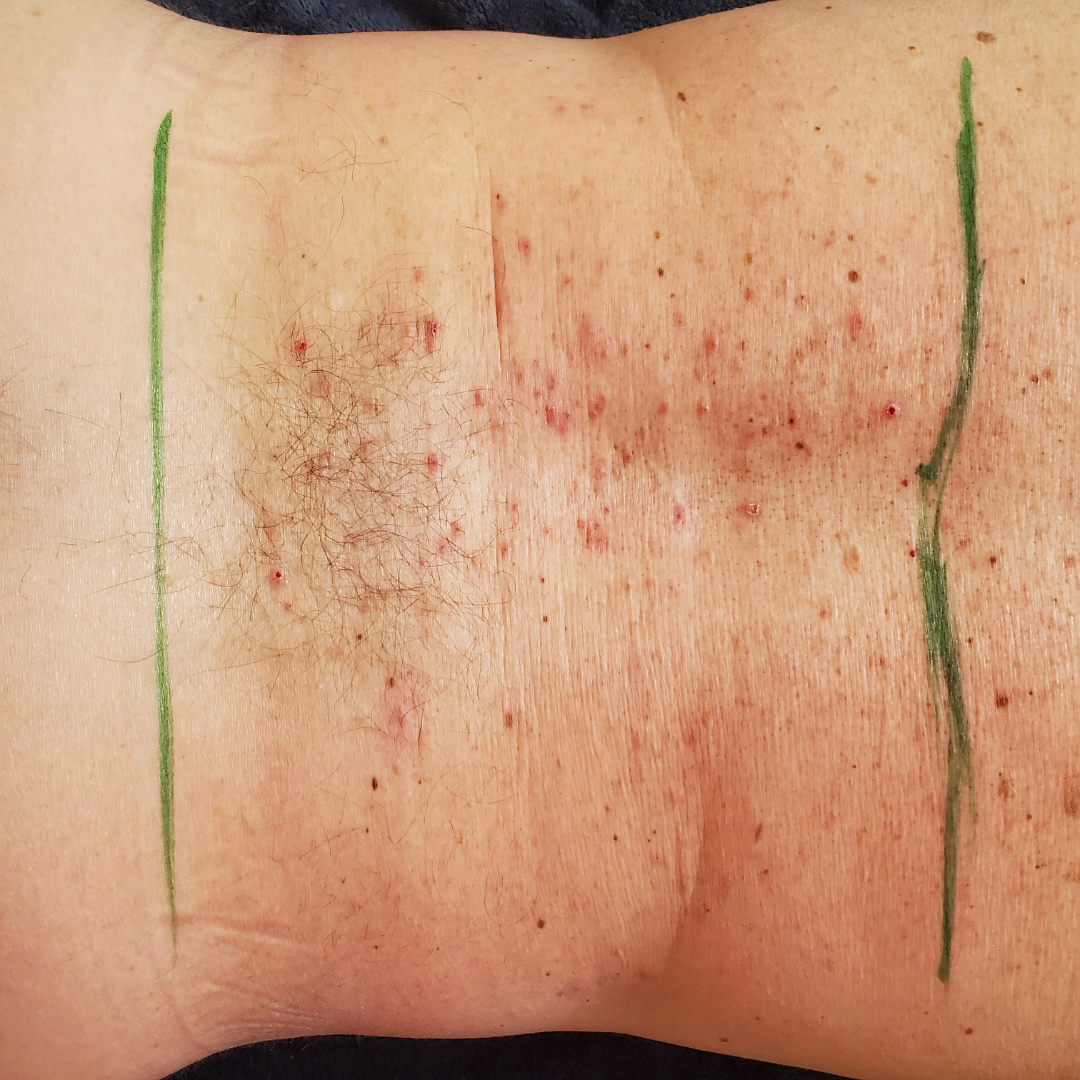Review: No differential diagnosis could be assigned on photographic review. Patient information: Located on the back of the torso. The patient also reports fatigue. Texture is reported as raised or bumpy and fluid-filled. Self-categorized by the patient as a rash. Reported duration is one to three months. The photograph was taken at an angle.